A skin lesion imaged with a dermatoscope: 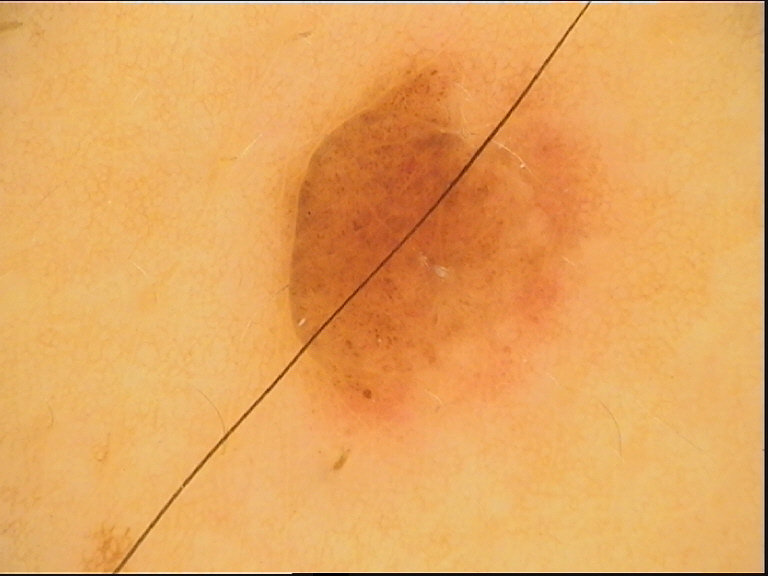Summary:
This is a banal lesion.
Conclusion:
Consistent with a compound nevus.